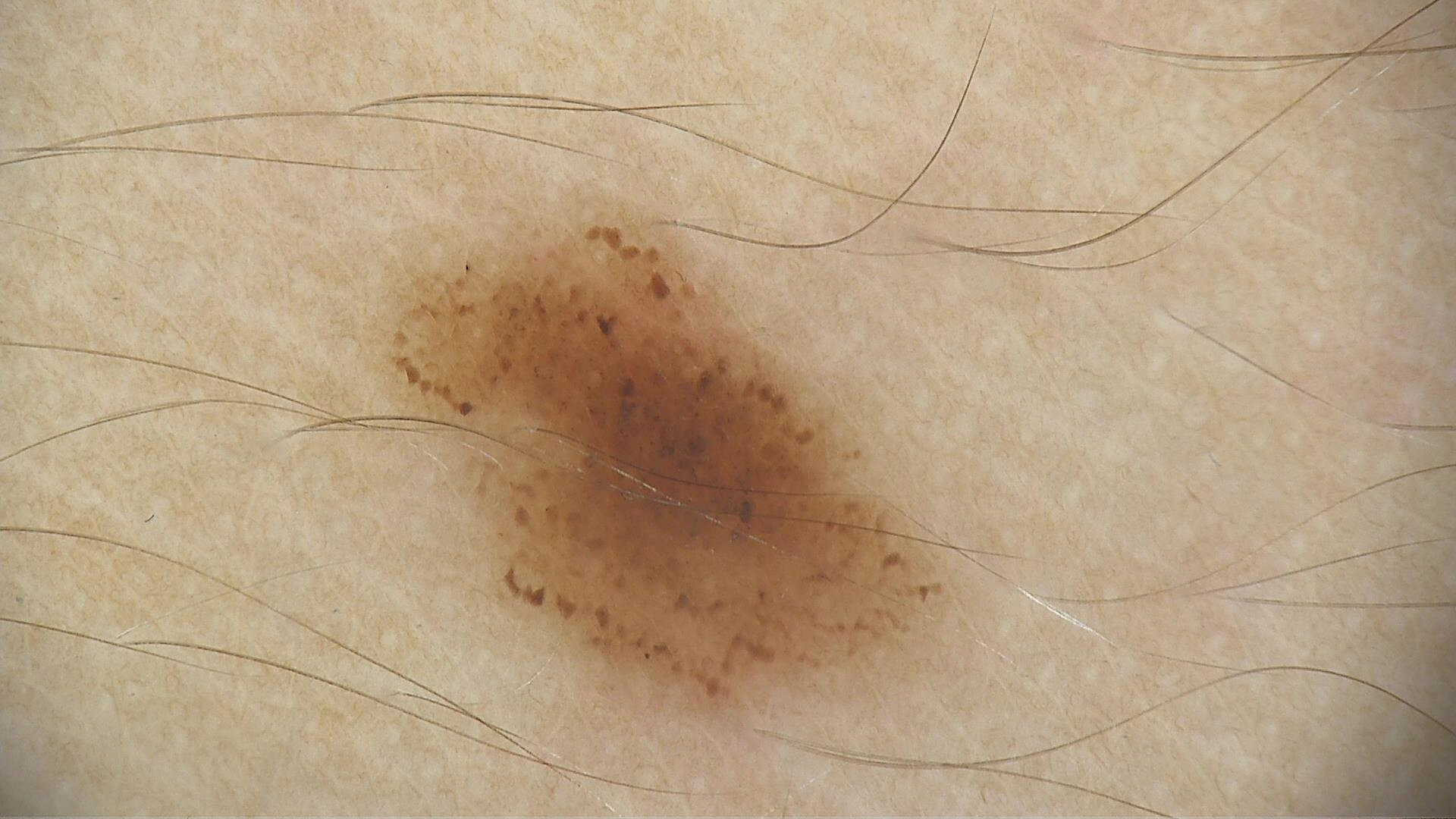{"image": "dermatoscopy", "diagnosis": {"name": "dysplastic junctional nevus", "code": "jd", "malignancy": "benign", "super_class": "melanocytic", "confirmation": "expert consensus"}}